This image was taken at an angle; the leg is involved: 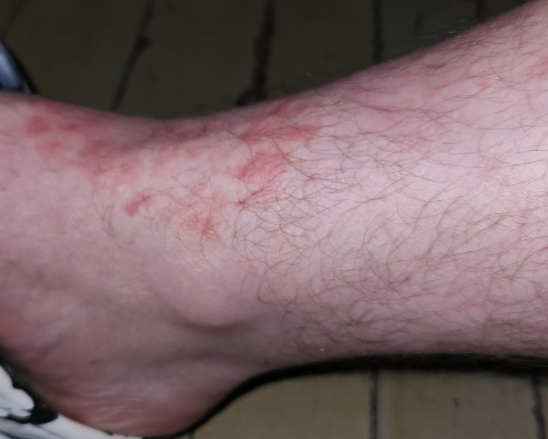Review: One reviewing dermatologist: Eczema and Allergic Contact Dermatitis were considered with similar weight.